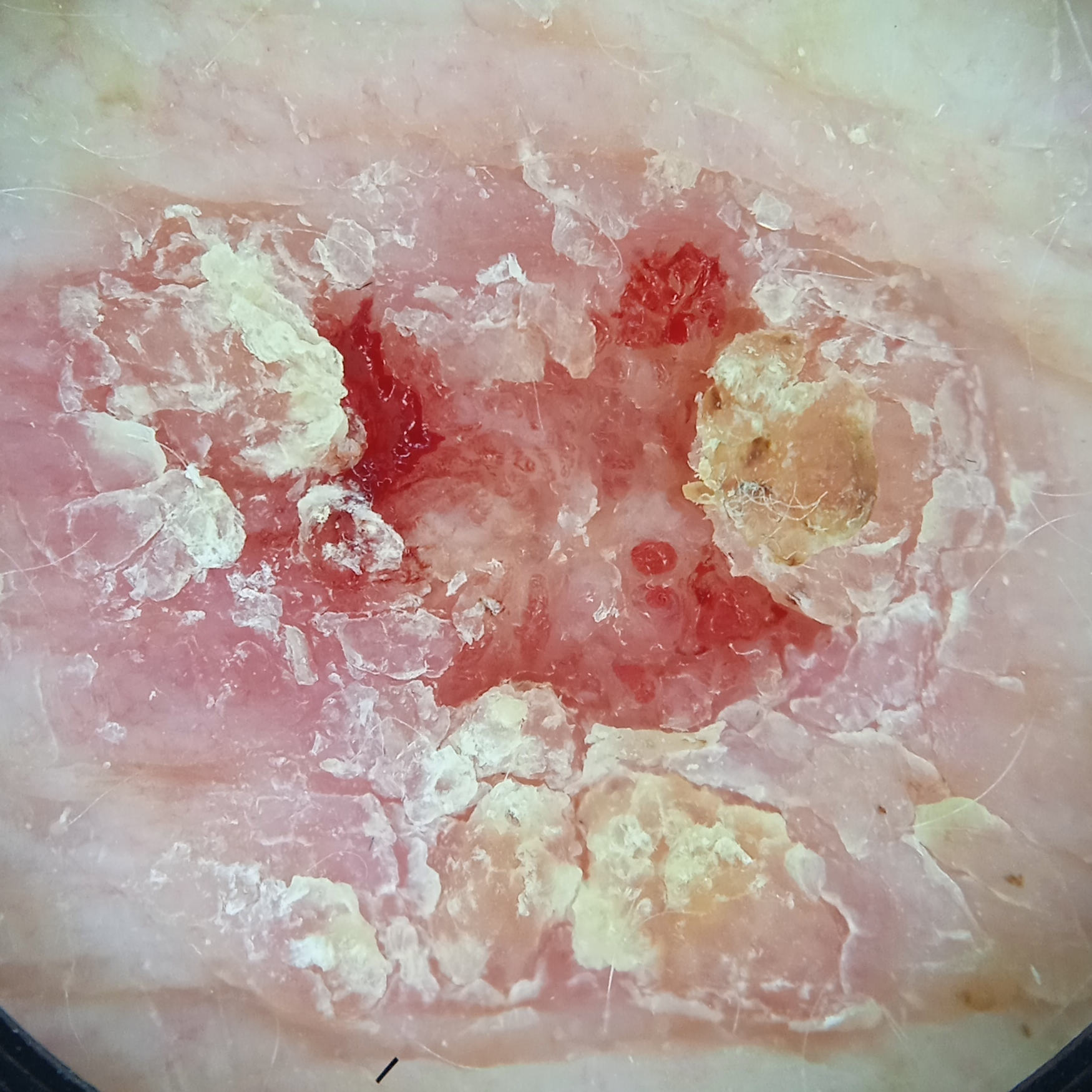Summary:
A male patient aged 83. A skin lesion imaged with a dermatoscope. Referred with a clinical suspicion of Bowen's disease. The patient says their skin reddens with sun exposure. Located on the torso. The lesion measures approximately 14.5 mm.
Assessment:
Four dermatologists reviewed the lesion; the consensus was a squamous cell carcinoma; diagnostic confidence was good.